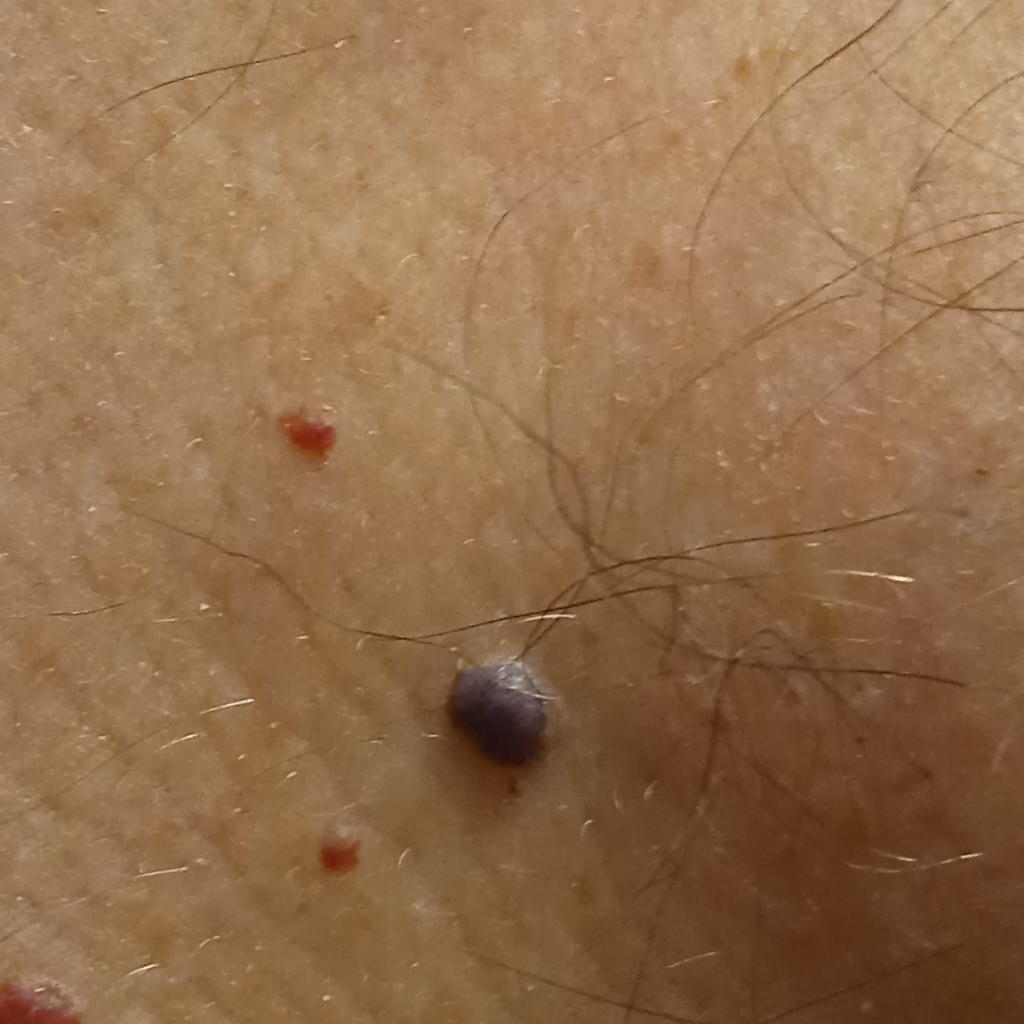Findings:
* subject — male, 72 years old
* nevus count — few melanocytic nevi overall
* relevant history — a personal history of cancer
* modality — clinical photograph
* body site — the torso
* lesion size — 4.7 mm
* diagnostic label — angioma (dermatologist consensus)